The patient is Fitzpatrick III · by history, prior malignancy (patient or family) · a female patient 52 years of age — 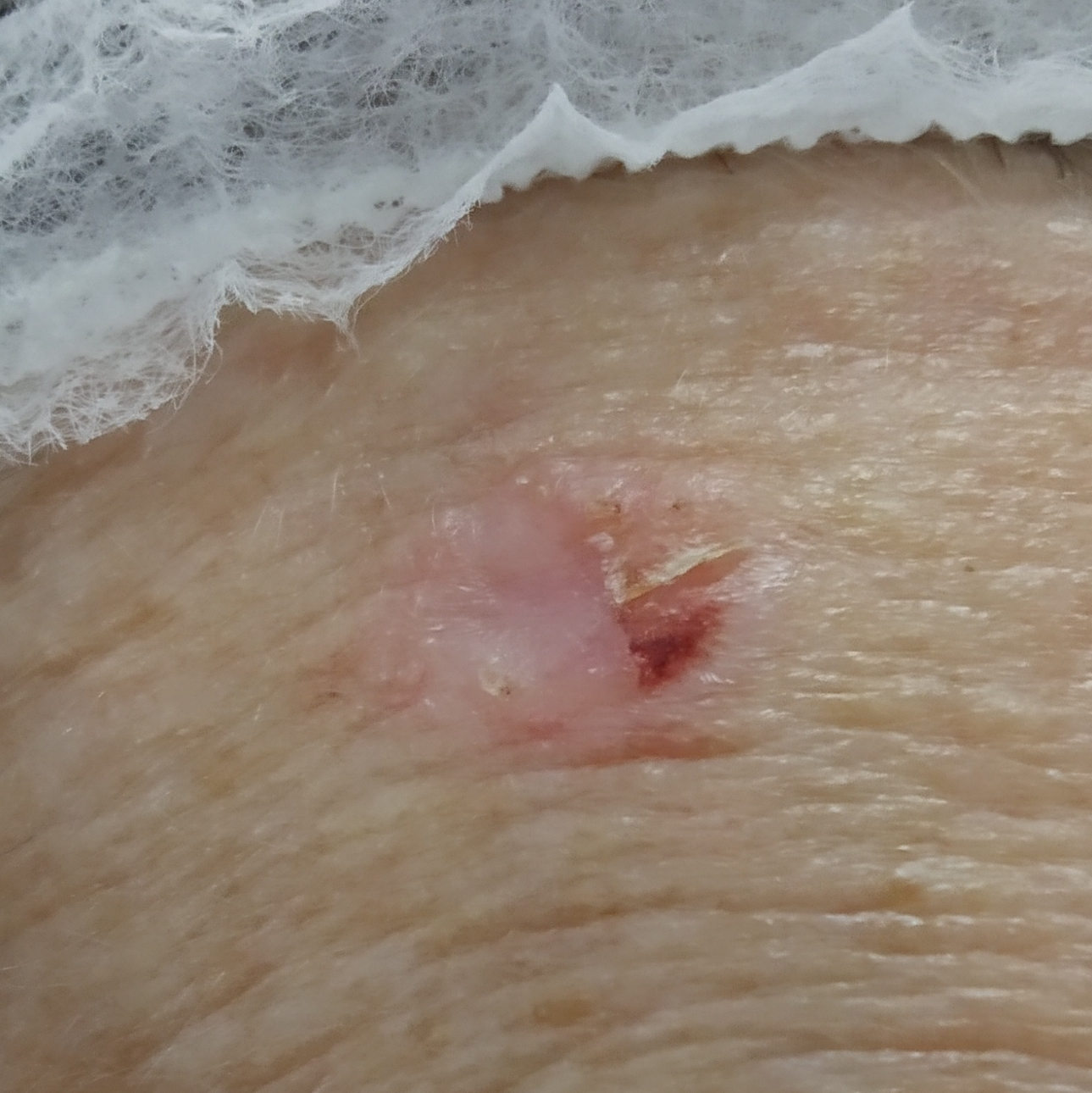site: the face; symptoms: elevation, itching, bleeding / no pain; diagnostic label: basal cell carcinoma (biopsy-proven).